Female patient, age 40–49 · located on the back of the torso · an image taken at an angle — 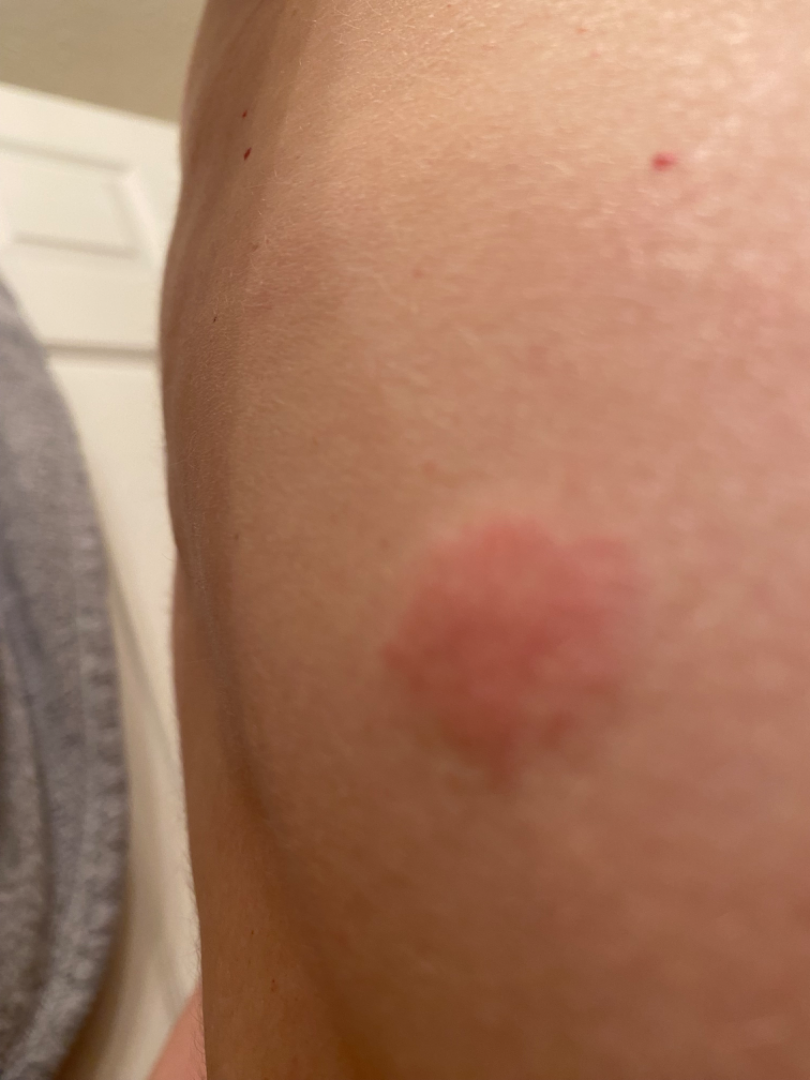Reviewed remotely by three dermatologists: most likely Insect Bite; with consideration of Urticaria; less probable is Primary cutaneous lymphoma; less likely is Cutaneous lupus.